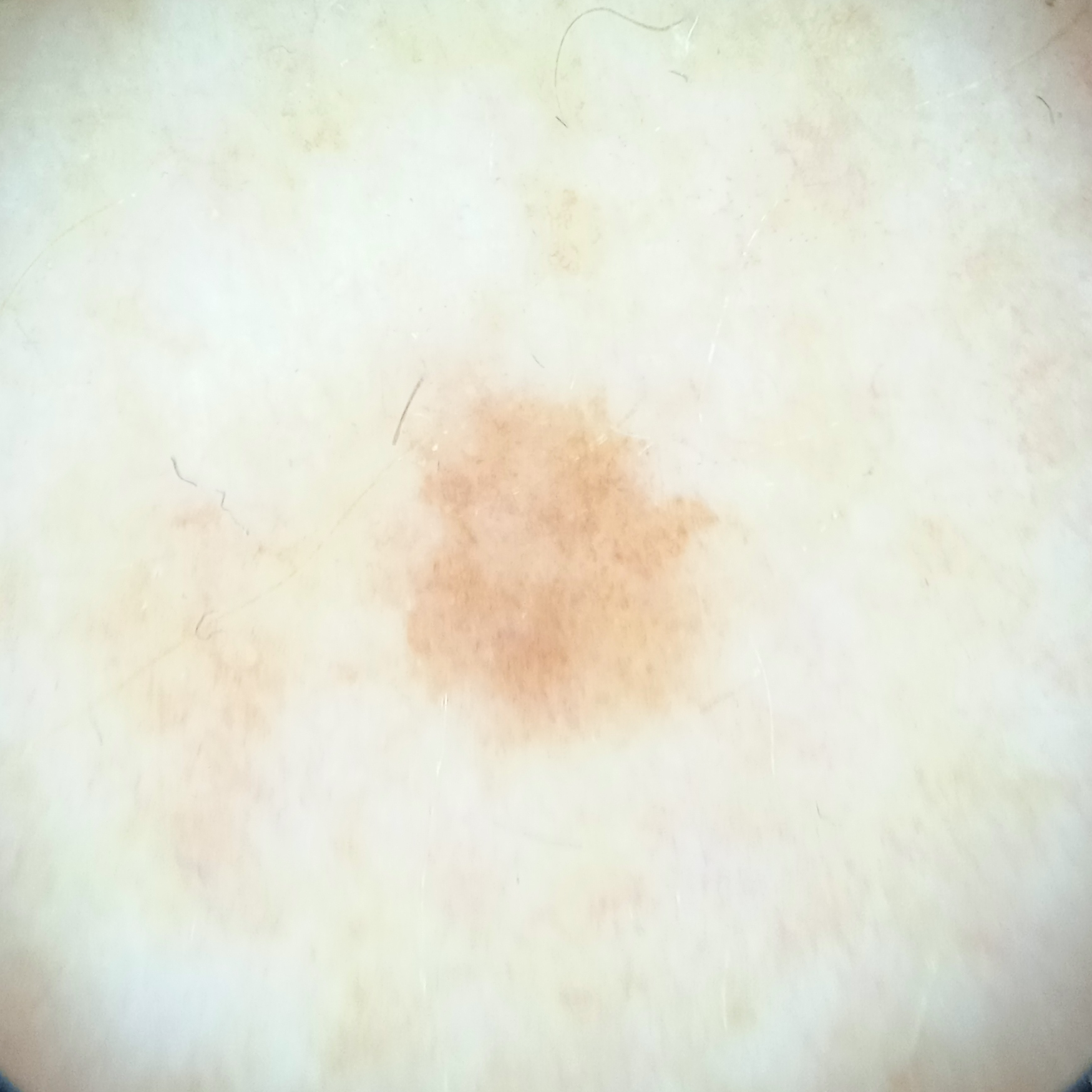patient: female, 53 years old; image type: dermatoscopic image; clinical context: research study (no referral diagnosis); anatomic site: a leg; lesion size: 4.1 mm; diagnosis: melanocytic nevus (dermatologist consensus).